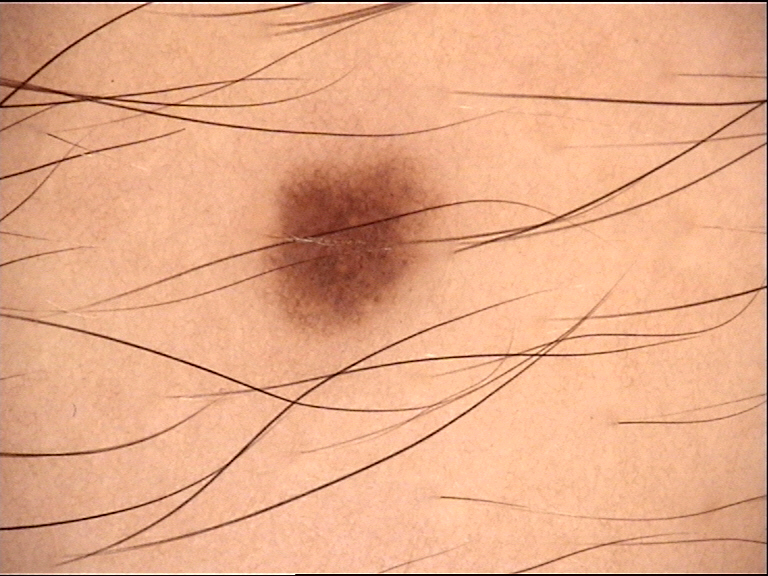A dermoscopic photograph of a skin lesion. Consistent with a banal lesion — a junctional nevus.